The subject is a male aged 63 to 67; dermoscopy of a skin lesion:
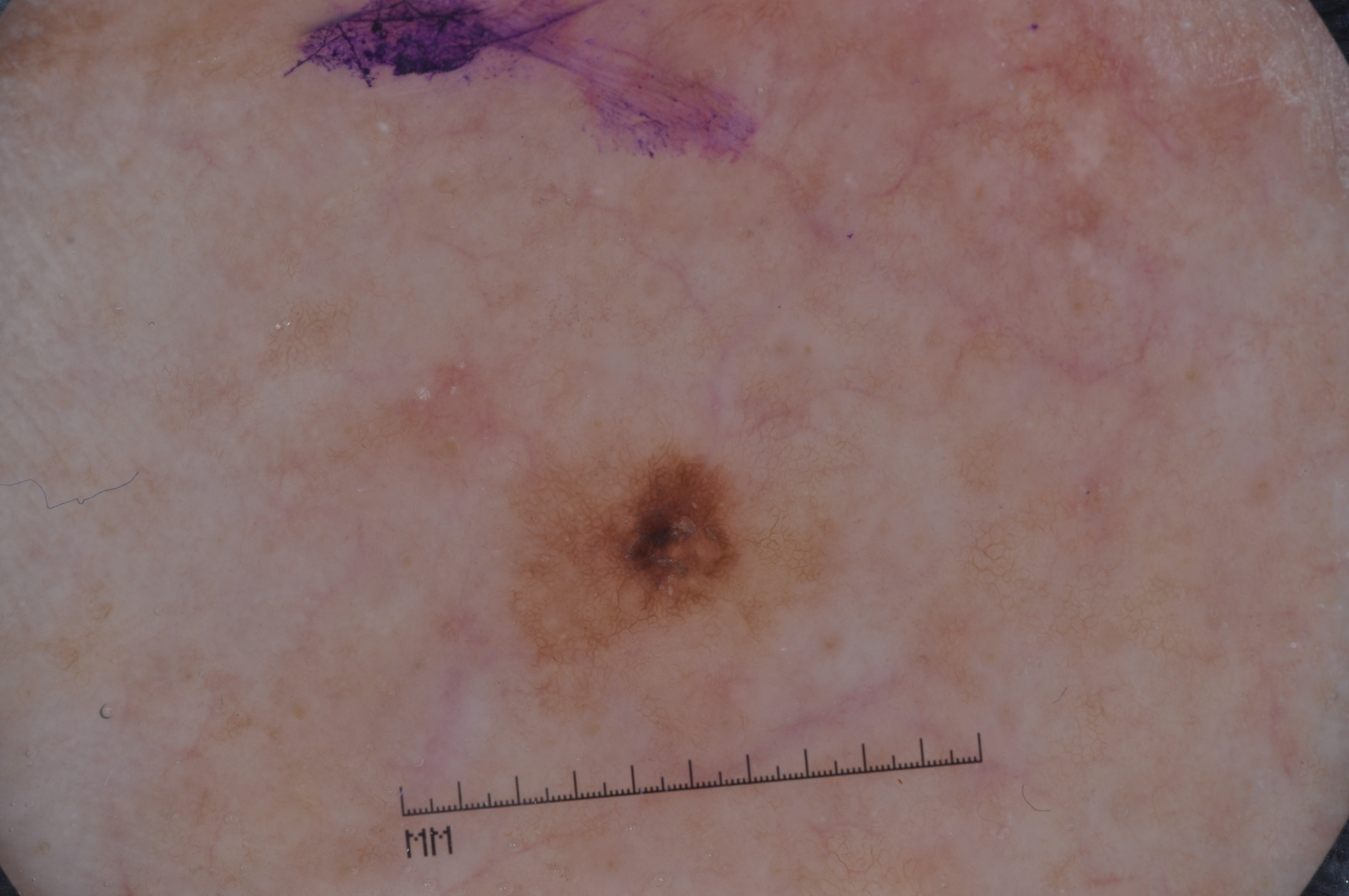On dermoscopy, the lesion shows pigment network. The lesion covers approximately 4% of the dermoscopic field. The lesion occupies the region (493, 445, 752, 699). Consistent with a melanocytic nevus.